Located on the arm · the patient did not report lesion symptoms · an image taken at a distance · the condition has been present for less than one week · the patient reports the lesion is raised or bumpy · female patient, age 50–59.
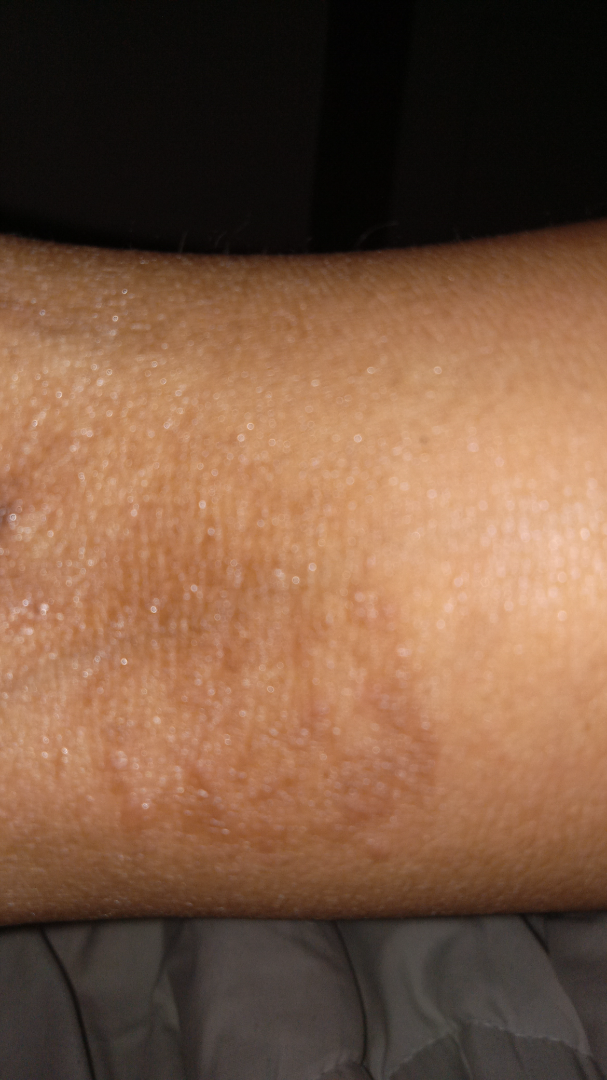impression = reviewed remotely by three dermatologists: the differential is split between Lichenified eczematous dermatitis and Chronic dermatitis; less likely is Tinea; less probable is Eczema; a more distant consideration is Post-Inflammatory hyperpigmentation.